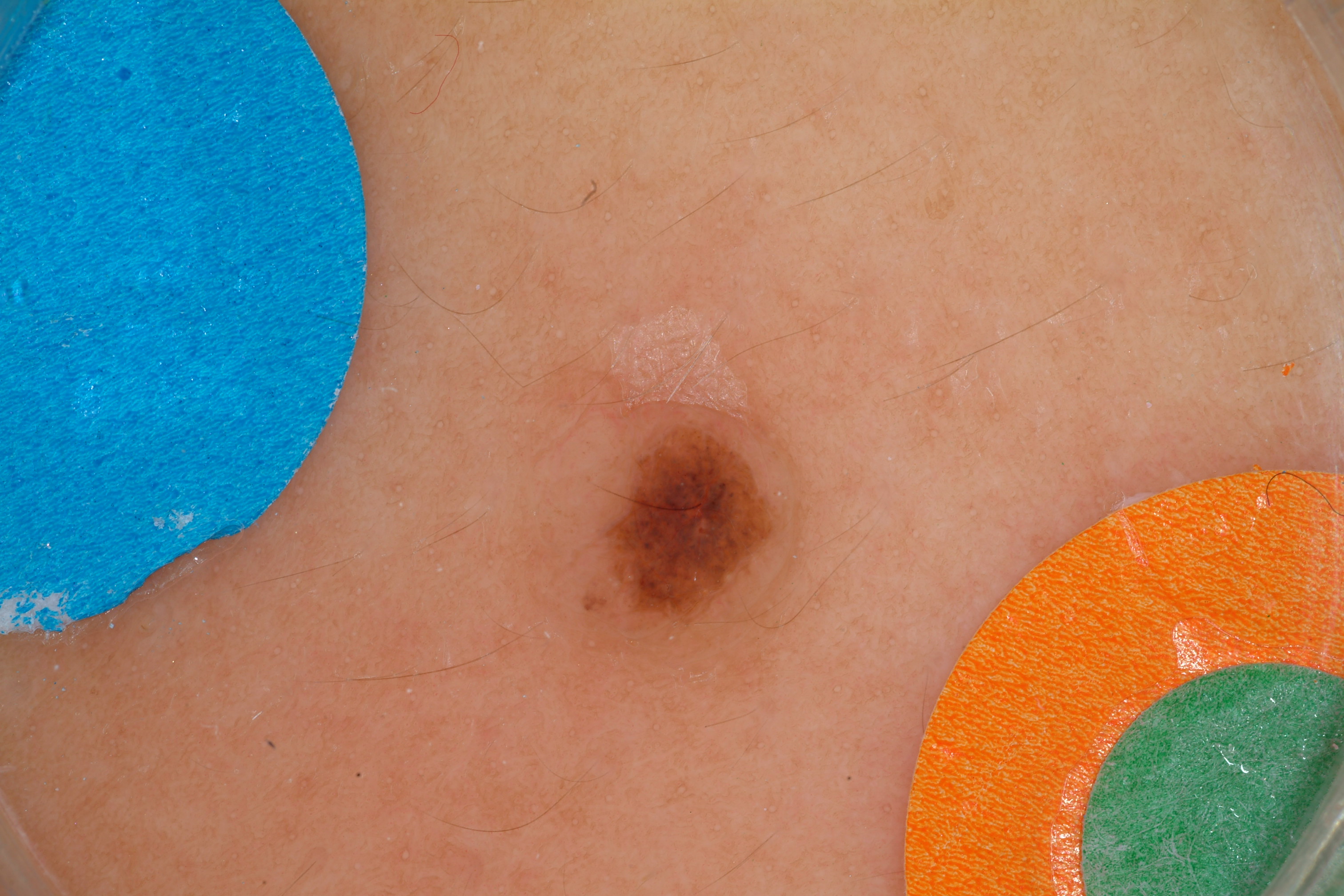A male subject, aged 13-17. This is a dermoscopic photograph of a skin lesion. Dermoscopic examination shows globules, with no streaks, pigment network, negative network, or milia-like cysts. The lesion occupies the region left=513, top=403, right=801, bottom=644. The diagnostic assessment was a melanocytic nevus, a benign skin lesion.